The affected area is the head or neck and arm. Female patient, age 50–59. The photo was captured at a distance — 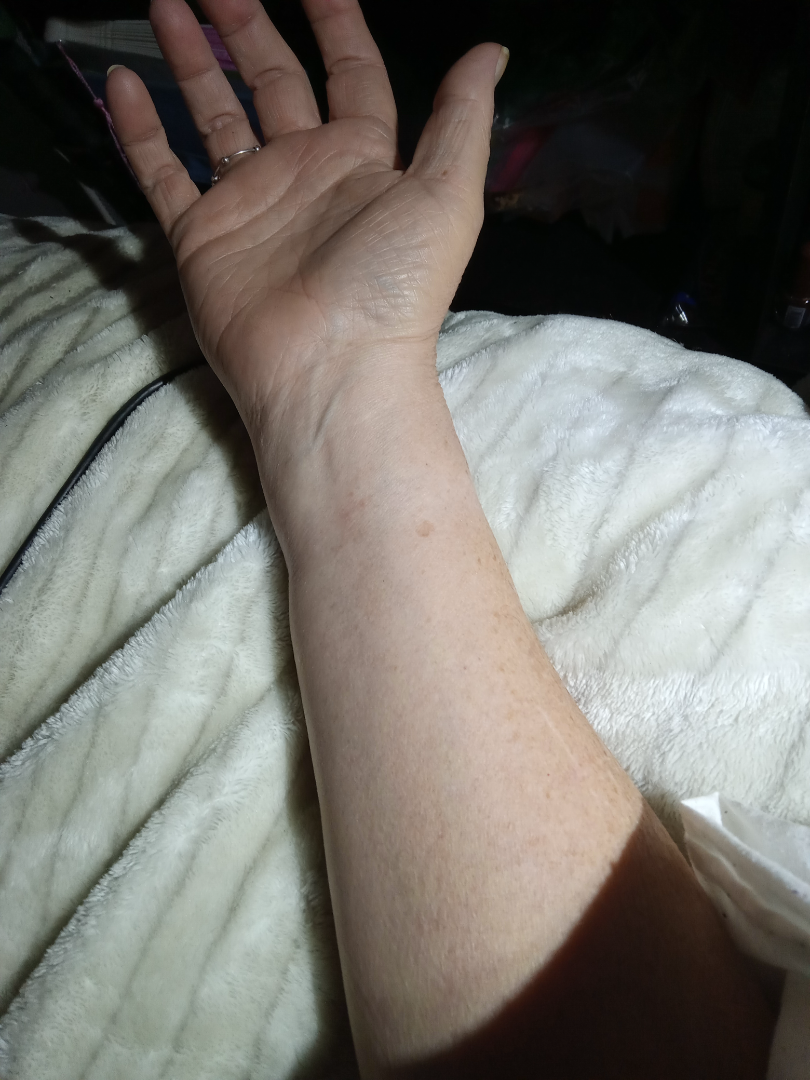Findings: Eczema (considered); Hypersensitivity (considered); Allergic Contact Dermatitis (considered).